A dermatoscopic image of a skin lesion: 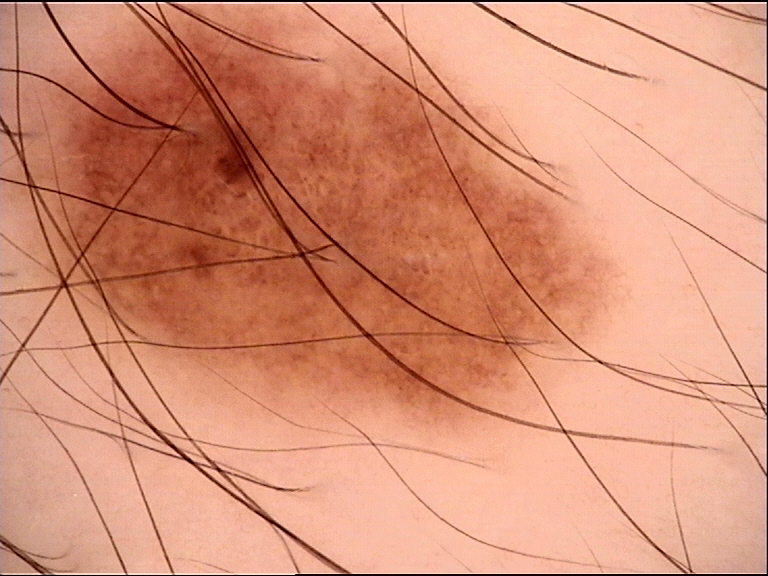| feature | finding |
|---|---|
| diagnosis | dysplastic junctional nevus (expert consensus) |